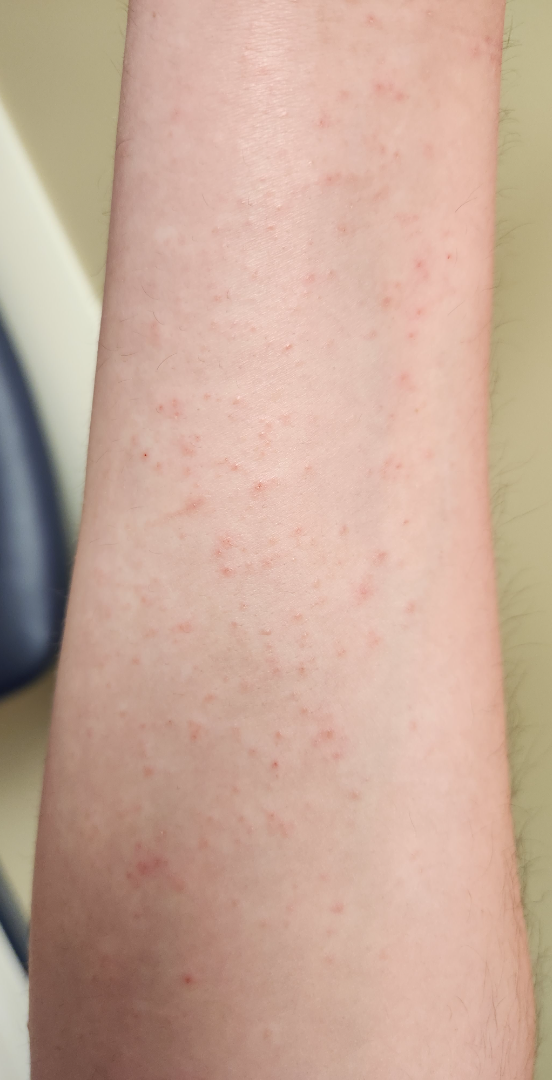Notes:
• dermatologist impression: the leading consideration is Allergic Contact Dermatitis; possibly Folliculitis; also consider Insect Bite